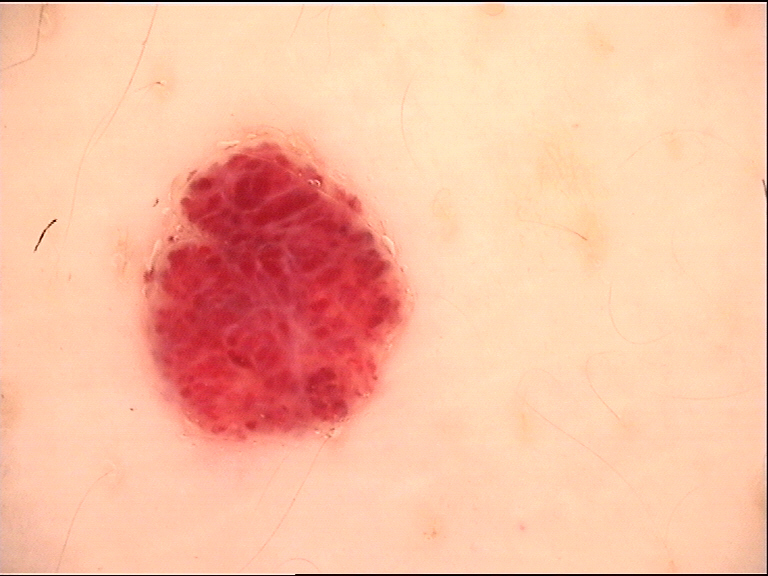Labeled as a hemangioma.